The lesion involves the front of the torso and back of the torso. The photograph was taken at a distance: 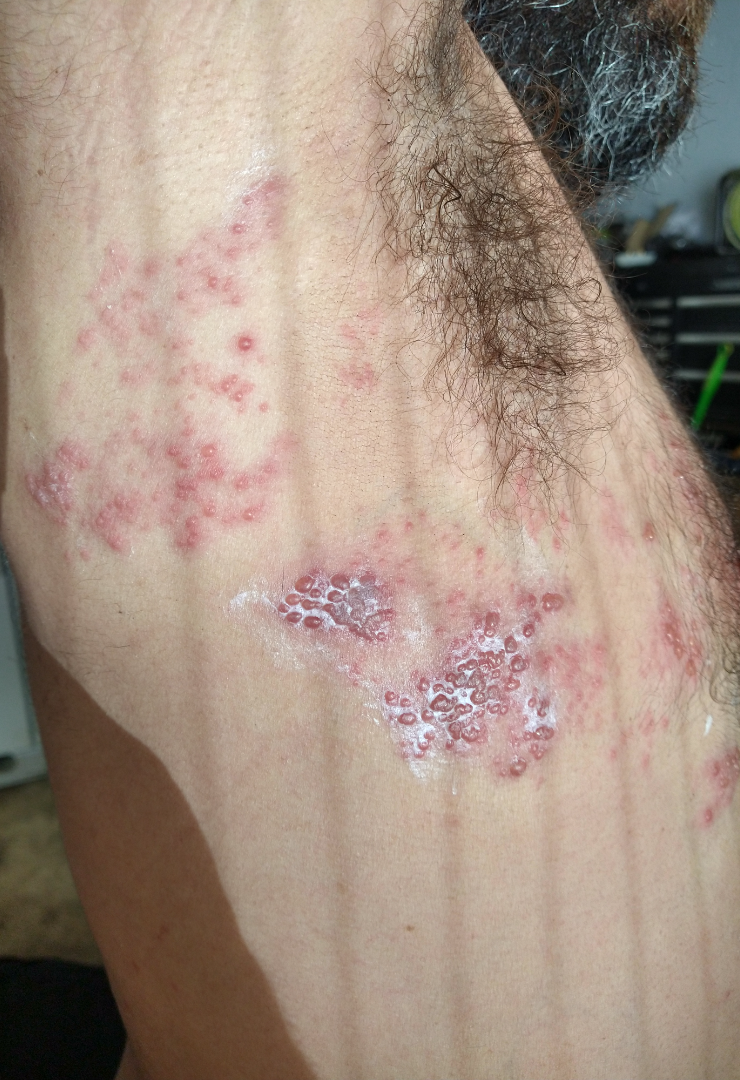Impression: The dermatologist could not determine a likely condition from the photograph alone.